A male patient aged around 75.
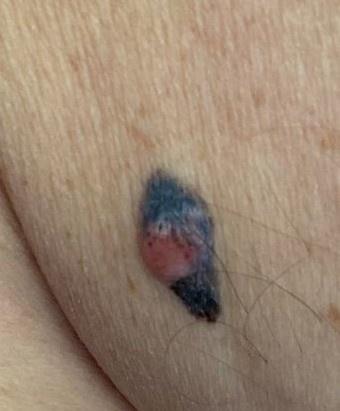Case summary: The lesion involves the trunk (the posterior trunk). Conclusion: Histopathology confirmed a melanoma.